A skin lesion imaged with a dermatoscope.
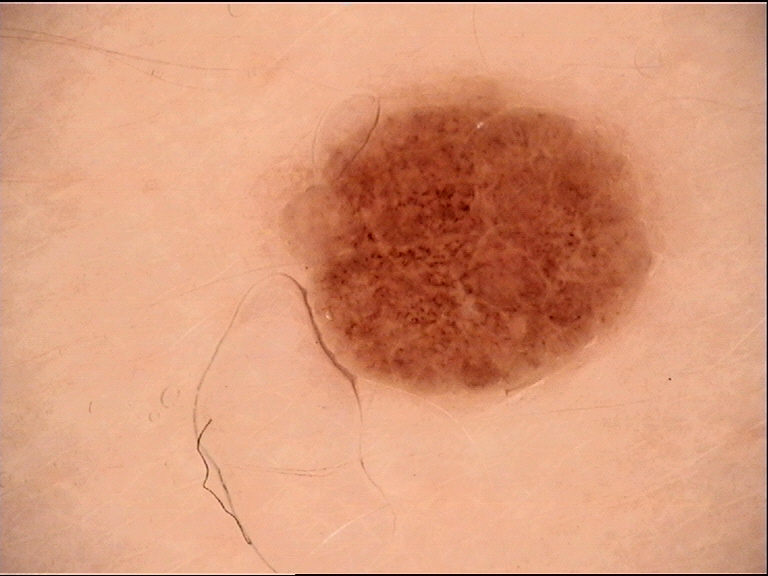Case:
- classification · banal
- assessment · compound nevus (expert consensus)